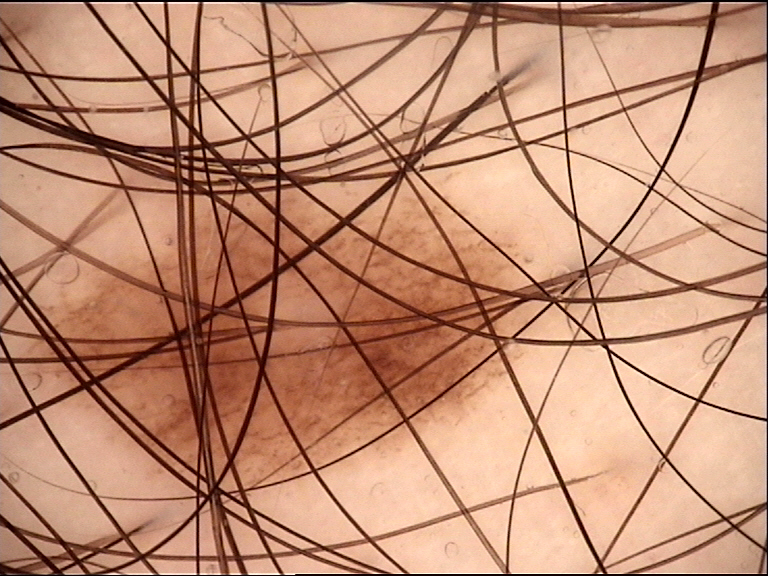A dermatoscopic image of a skin lesion. The diagnostic label was a dysplastic junctional nevus.